The affected area is the arm. The patient is a female aged 30–39. This image was taken at a distance.
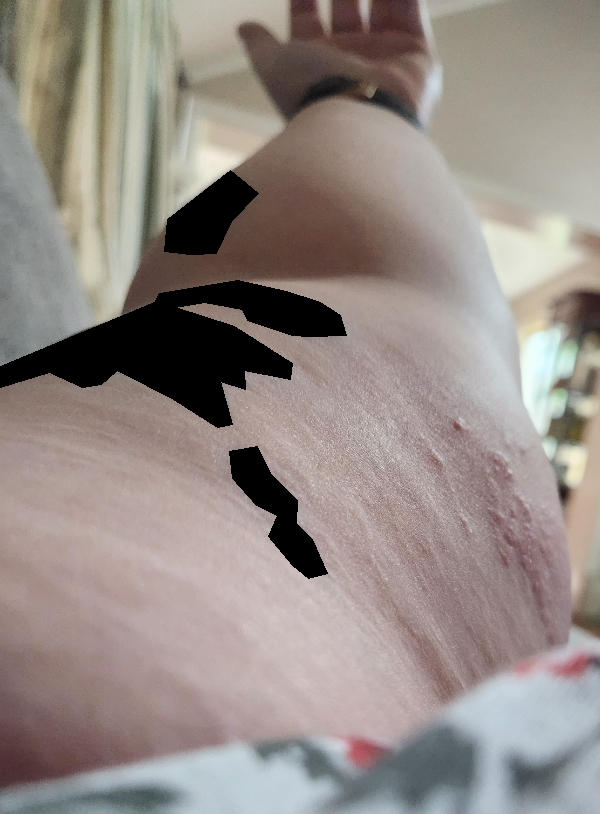Q: What is the lesion texture?
A: raised or bumpy
Q: When did this start?
A: one to four weeks
Q: How does the patient describe it?
A: a rash
Q: What symptoms does the patient report?
A: itching
Q: What is the dermatologist's impression?
A: Urticaria (primary); Eczema (possible); Allergic Contact Dermatitis (possible); Pruritic urticarial papules and plaques of pregnancy (remote); Scabies (remote)